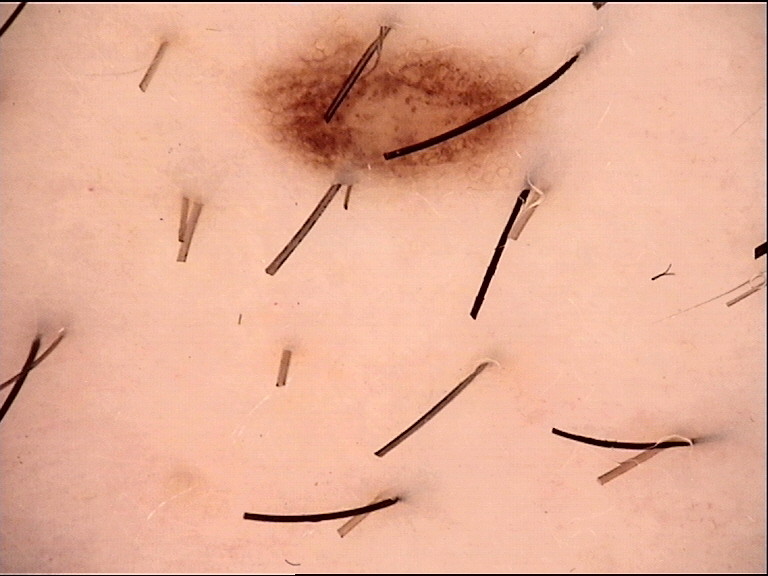Conclusion:
Diagnosed as a dysplastic junctional nevus.